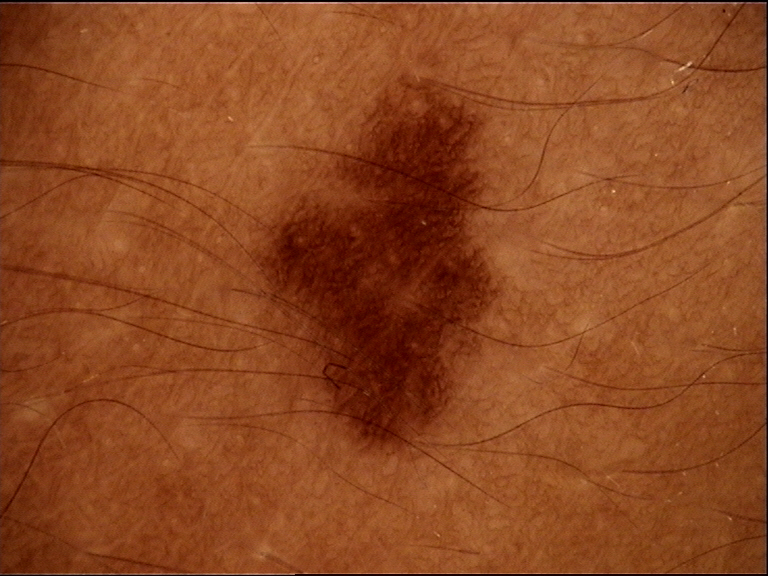Impression:
The diagnosis was a benign lesion — a dysplastic junctional nevus.